A skin lesion imaged with a dermatoscope. The subject is a female about 50 years old: 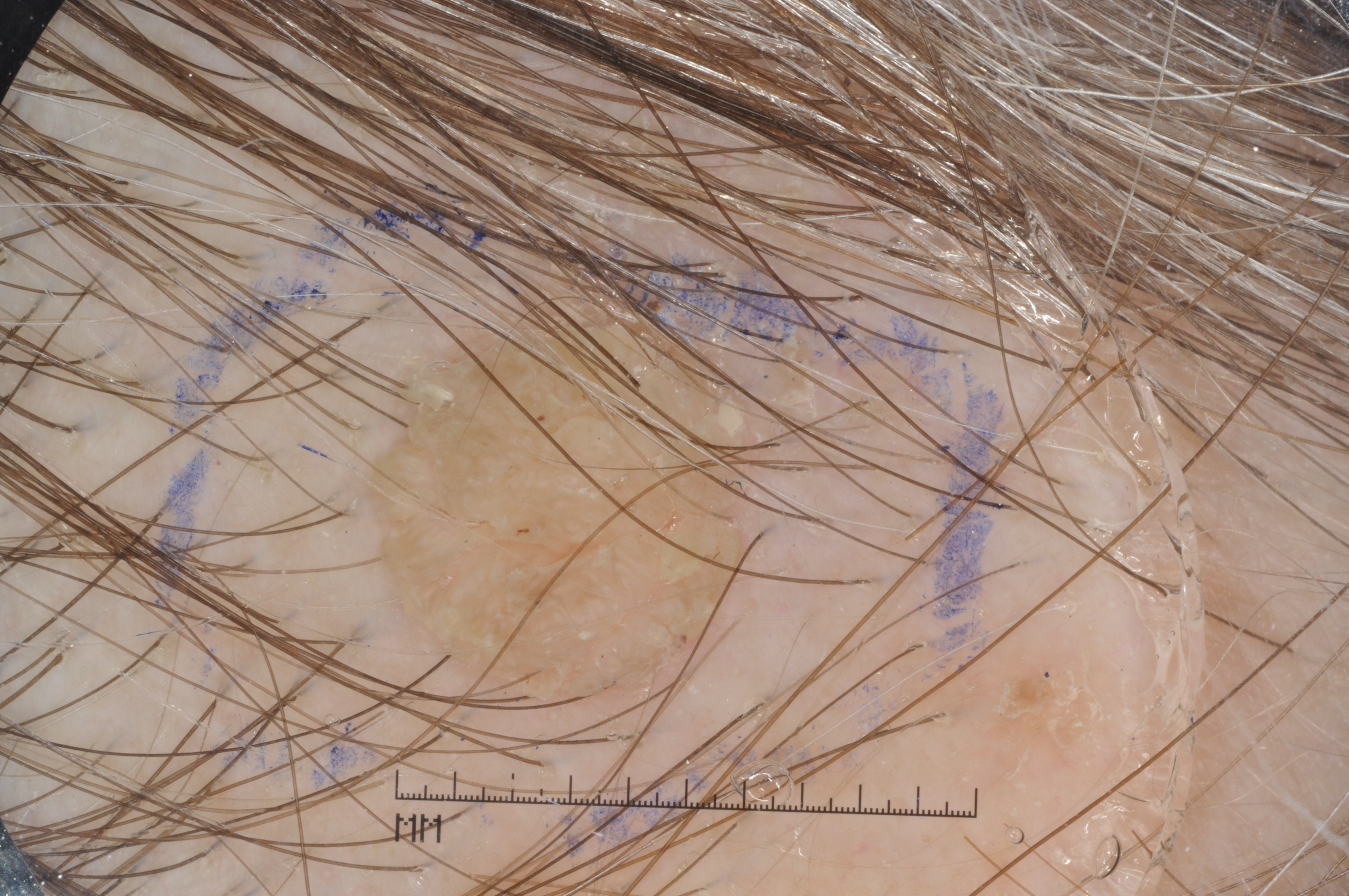{"dermoscopic_features": {"present": ["milia-like cysts"], "absent": ["negative network", "streaks", "pigment network"]}, "lesion_location": {"bbox_xyxy": [365, 277, 781, 710]}, "lesion_extent": {"approx_field_fraction_pct": 12}, "diagnosis": {"name": "seborrheic keratosis", "malignancy": "benign", "lineage": "keratinocytic", "provenance": "clinical"}}